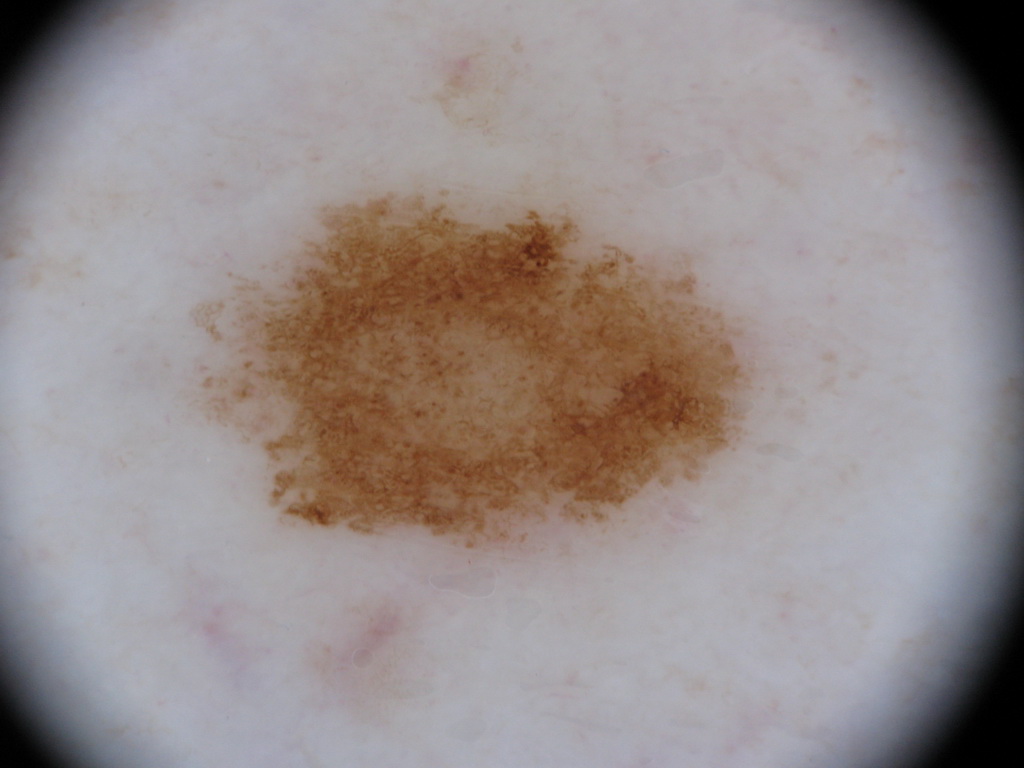{
  "image": {
    "modality": "dermoscopy"
  },
  "patient": {
    "sex": "female",
    "age_approx": 60
  },
  "lesion_location": {
    "bbox_xyxy": [
      192,
      179,
      755,
      557
    ]
  },
  "dermoscopic_features": {
    "present": [
      "pigment network"
    ],
    "absent": [
      "milia-like cysts",
      "streaks",
      "negative network",
      "globules"
    ]
  },
  "lesion_extent": "moderate",
  "diagnosis": {
    "name": "melanocytic nevus",
    "malignancy": "benign",
    "lineage": "melanocytic",
    "provenance": "clinical"
  }
}